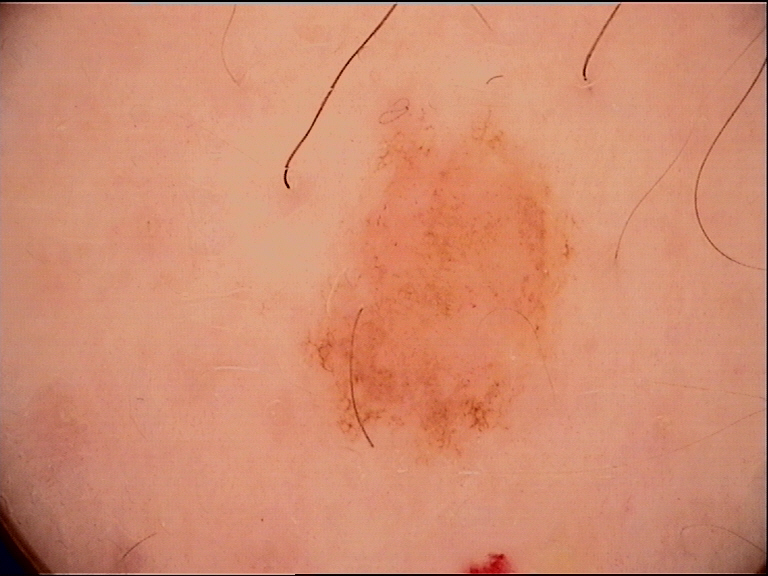A dermoscopy image of a single skin lesion. Diagnosed as a benign lesion — a dysplastic junctional nevus.